A dermoscopy image of a single skin lesion:
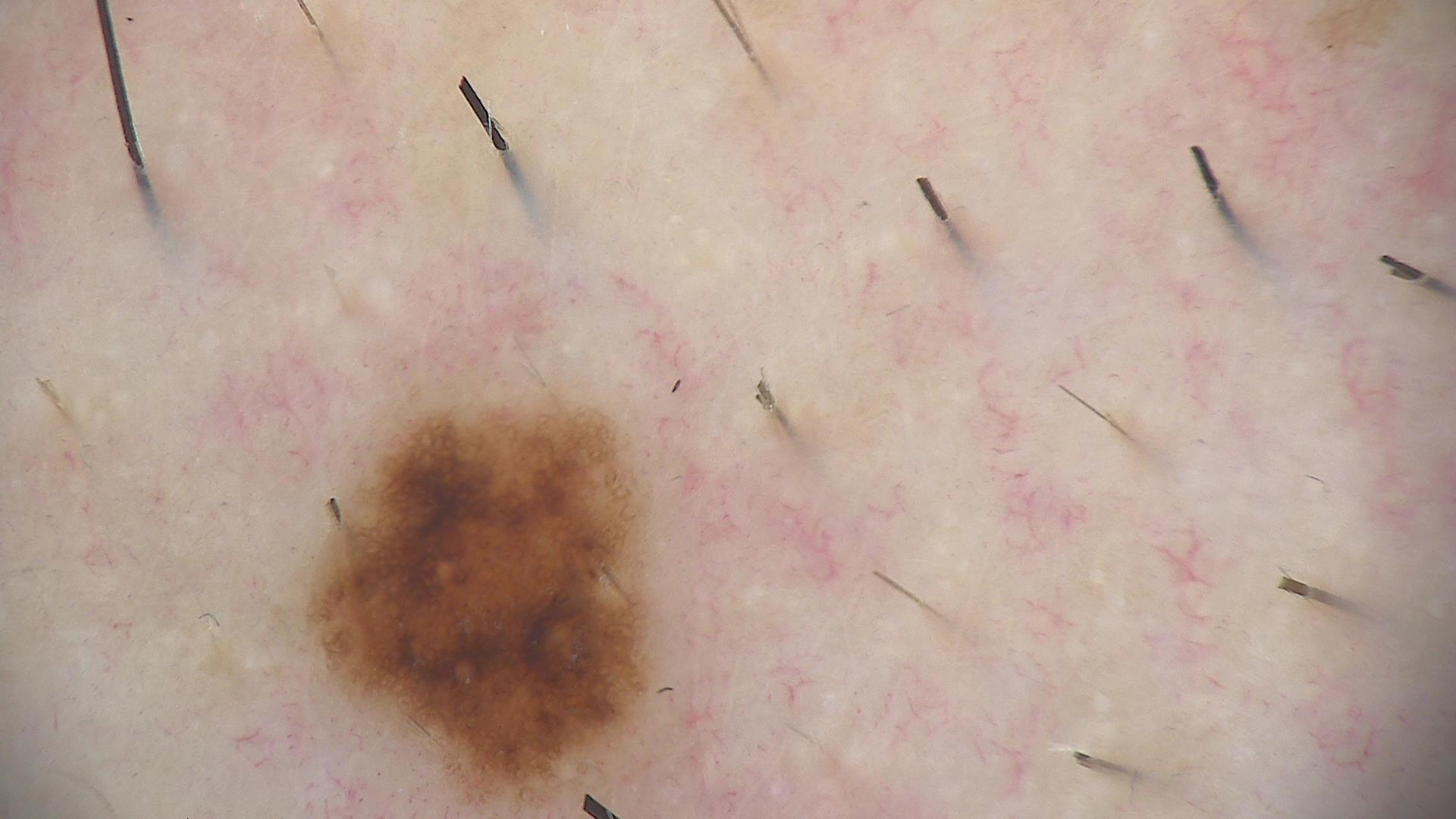diagnosis = dysplastic junctional nevus (expert consensus).